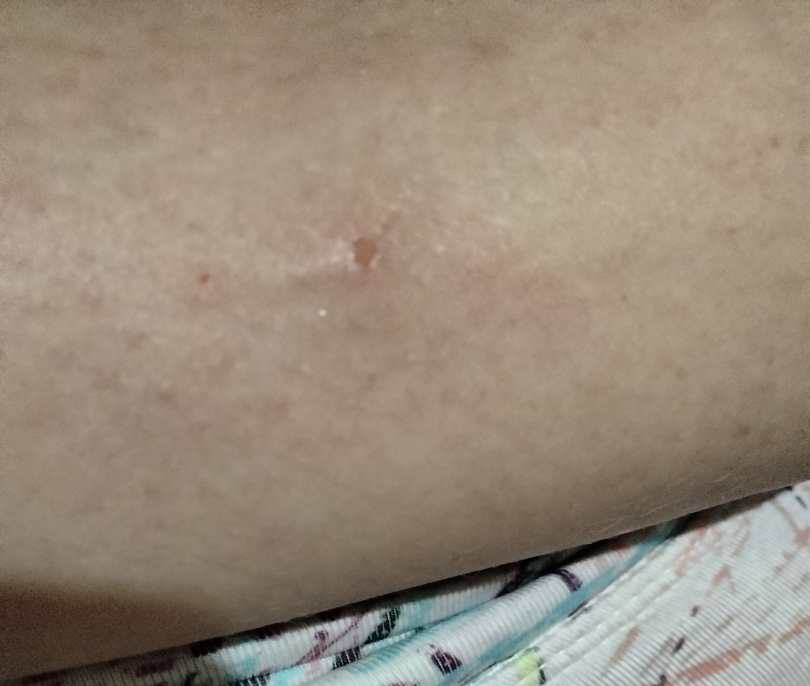Q: What is the framing?
A: at an angle
Q: Where on the body?
A: front of the torso
Q: What is the patient's skin tone?
A: Fitzpatrick phototype II
Q: What symptoms does the patient report?
A: itching, enlargement and bothersome appearance
Q: What is the lesion texture?
A: raised or bumpy
Q: Who is the patient?
A: female, age 40–49
Q: What is the dermatologist's impression?
A: the leading consideration is Folliculitis